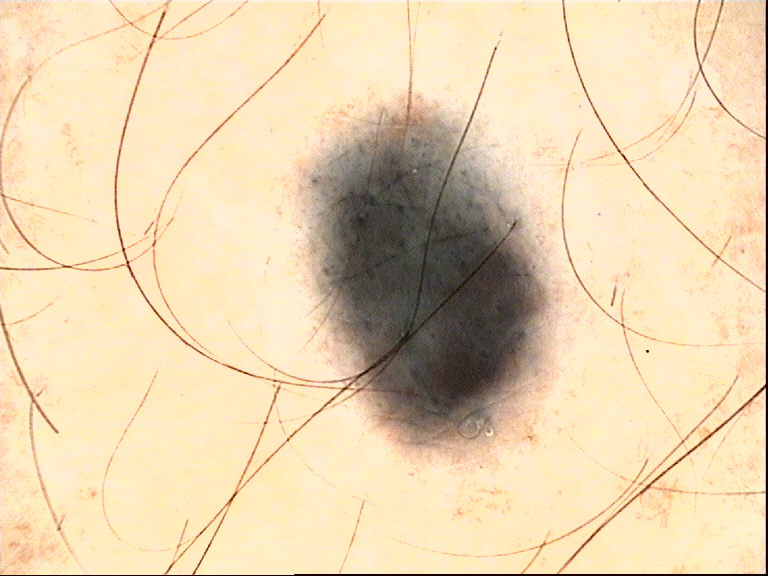imaging: dermoscopy | lesion type: dermal, banal | class: blue nevus (expert consensus).